A dermoscopic photograph of a skin lesion.
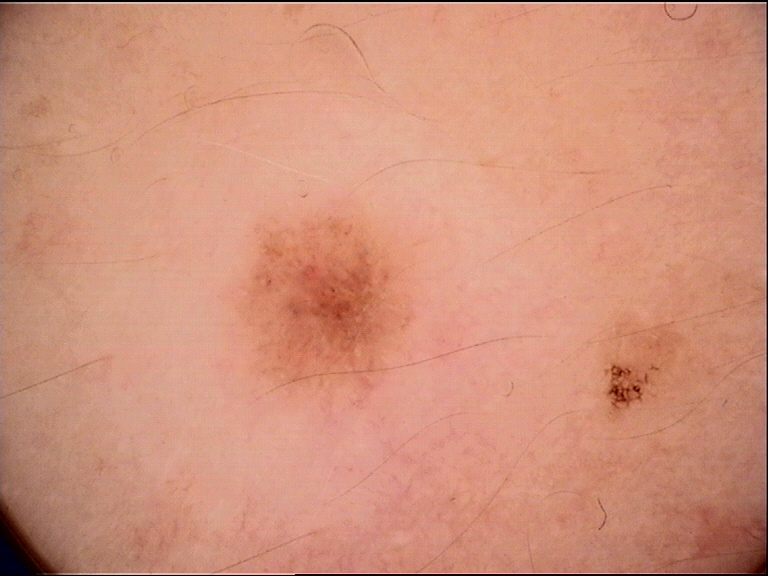class: dysplastic junctional nevus (expert consensus).